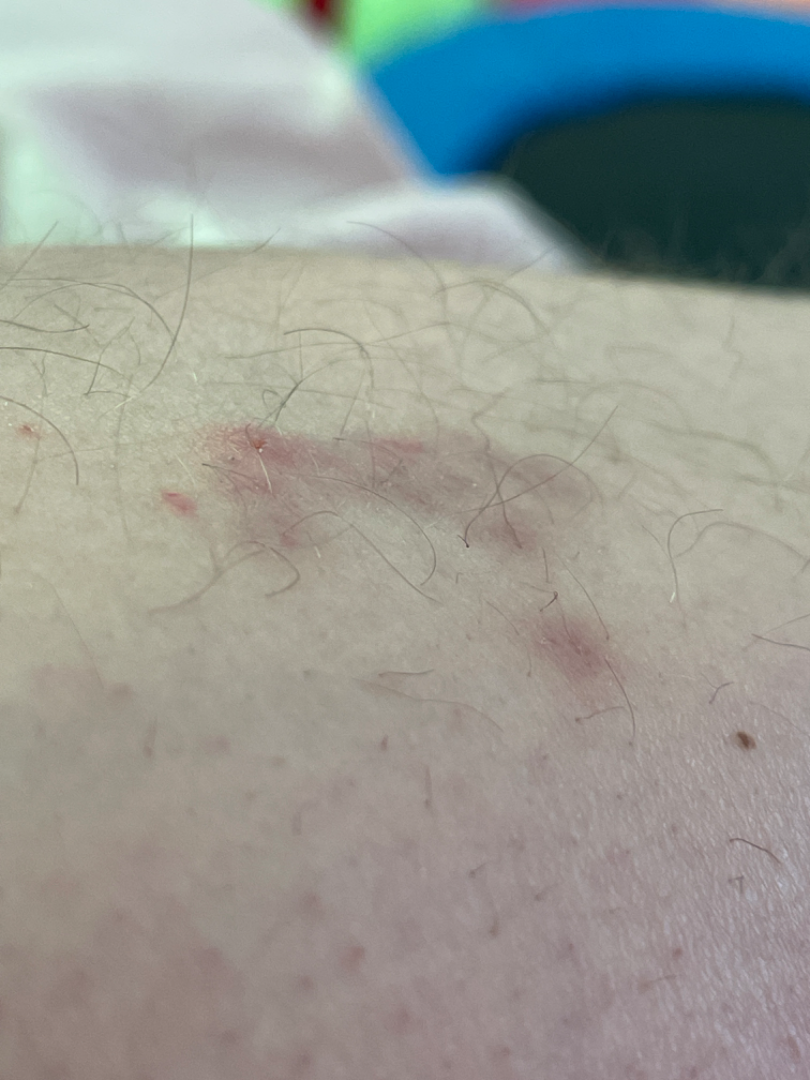The patient considered this a rash.
The lesion is described as rough or flaky.
The palm, top or side of the foot, sole of the foot and leg are involved.
This image was taken at an angle.
On photographic review, the primary impression is Herpes Simplex; also consider Eczema; less likely is Insect Bite.